A male patient in their mid-50s. The patient was assessed as Fitzpatrick phototype III. History notes prior skin cancer (patient or family). A clinical photo of a skin lesion taken with a smartphone — 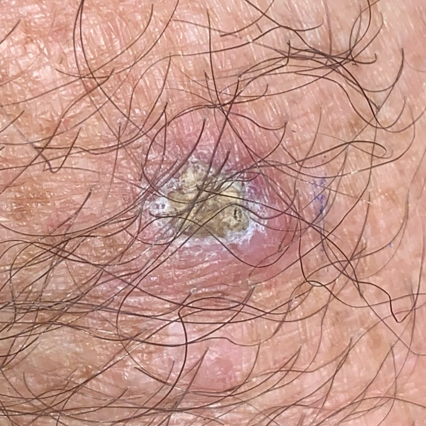Q: Where on the body is the lesion?
A: a forearm
Q: Lesion size?
A: approx. 15 × 10 mm
Q: What does the patient describe?
A: growth, itching, elevation, bleeding
Q: What is this lesion?
A: actinic keratosis (biopsy-proven)